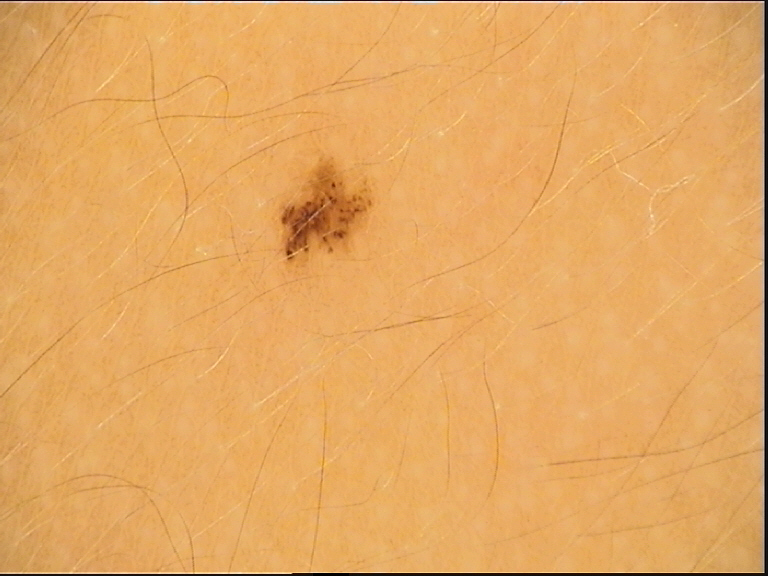image — dermoscopy; assessment — dysplastic junctional nevus (expert consensus).